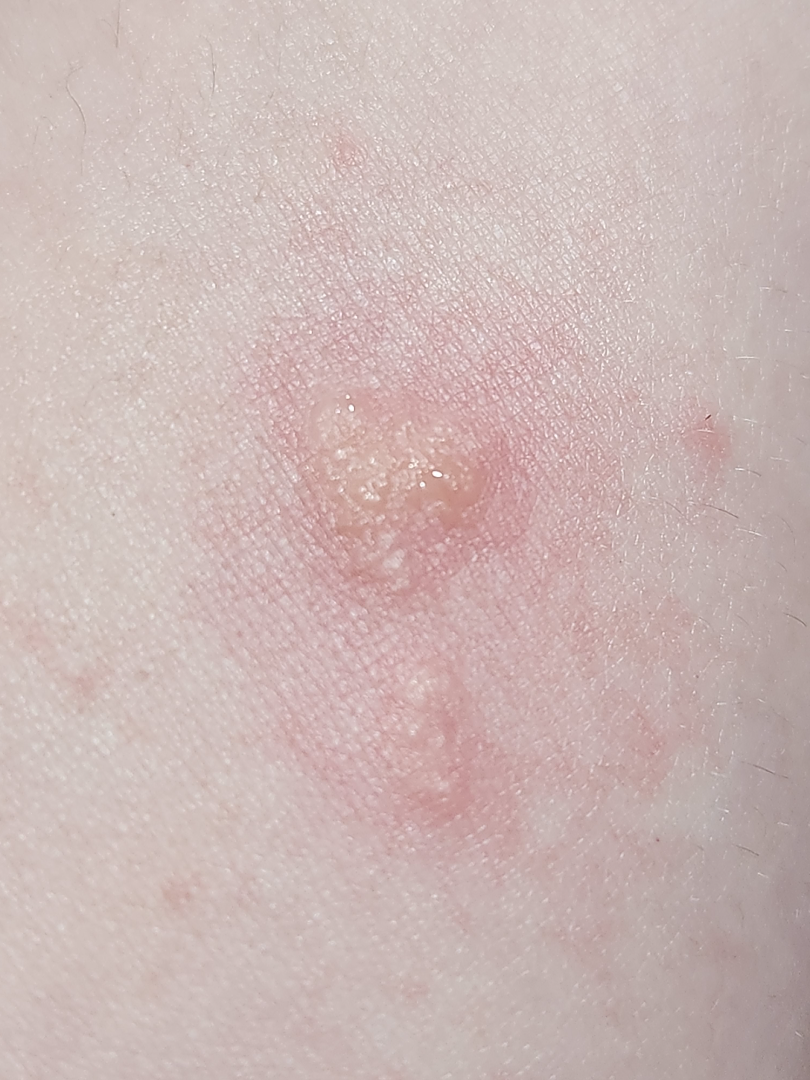Notes:
- differential · Blister (primary); Herpes Simplex (considered); Herpes Zoster (remote)